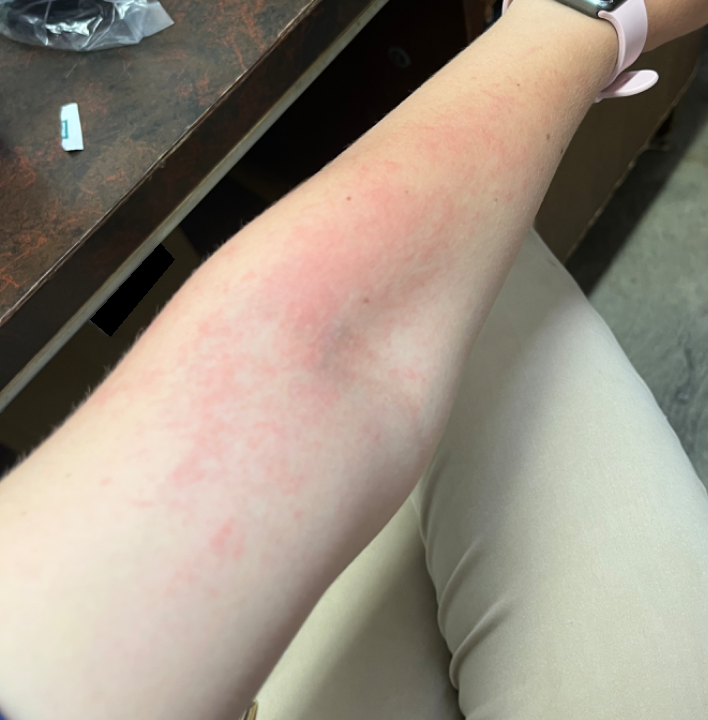Consistent with Acute dermatitis, NOS.